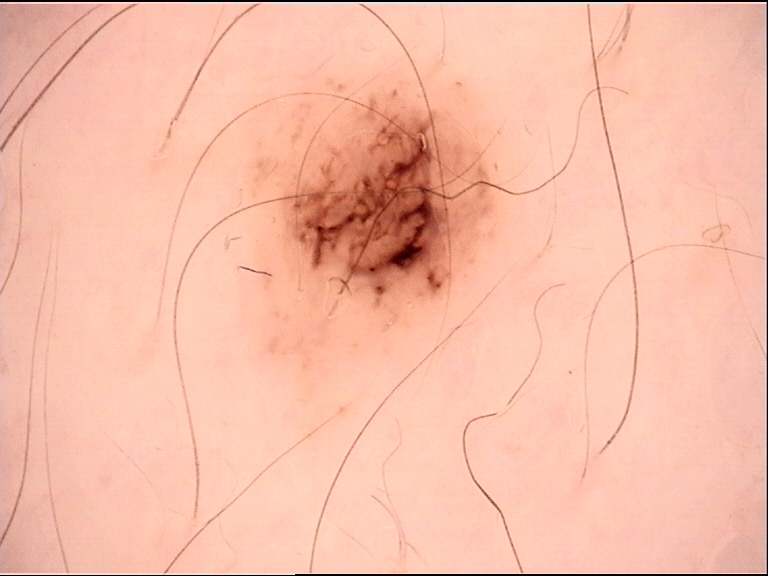A dermoscopy image of a single skin lesion.
The diagnostic label was a benign lesion — a dysplastic compound nevus.